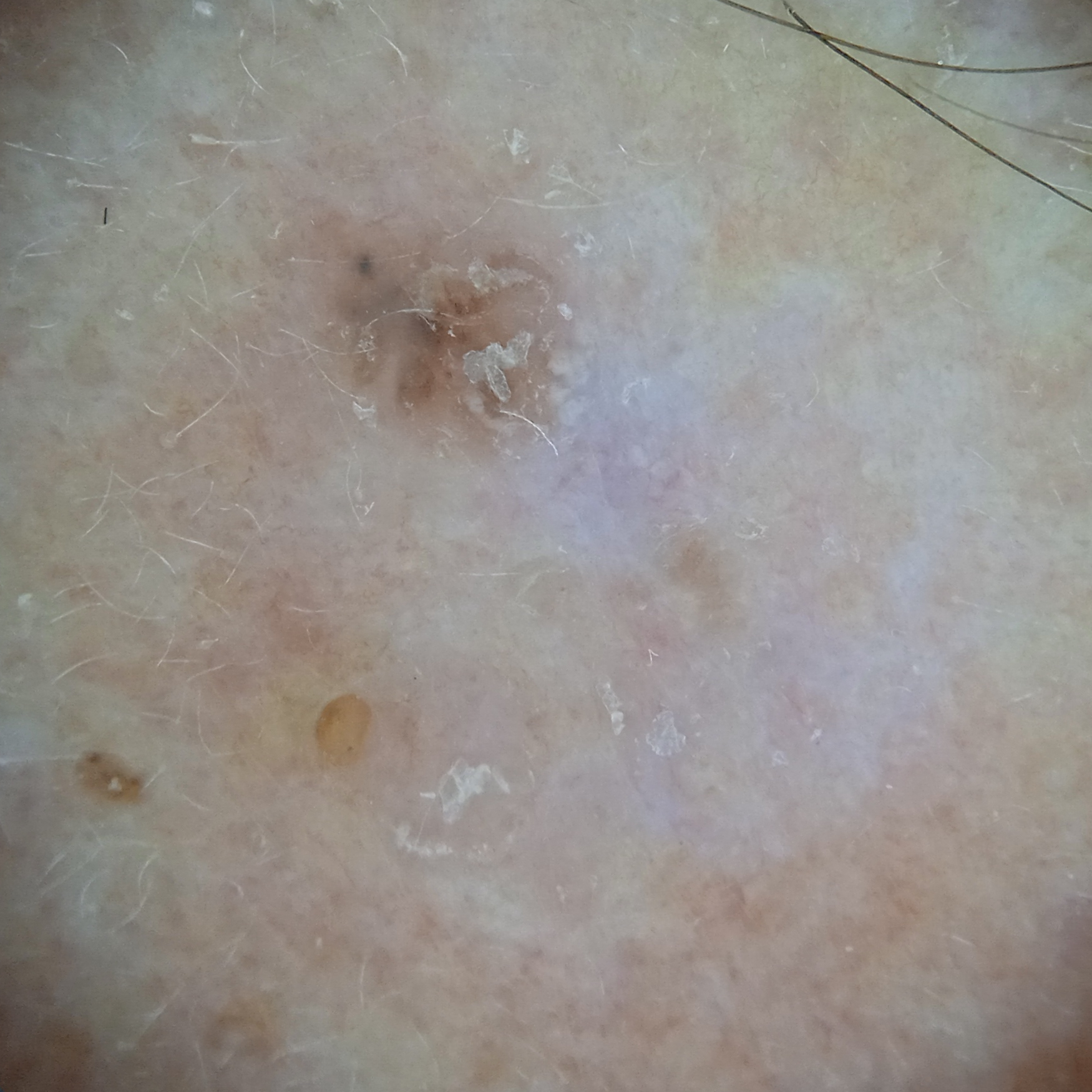Summary:
A female patient age 60. A dermoscopic image of a skin lesion. Few moles overall by the patient's own estimate. The referring clinician suspected basal cell carcinoma. The patient reports a personal history of cancer and a personal history of skin cancer. The lesion involves the face.
Pathology:
On biopsy, the diagnosis was a basal cell carcinoma, following excision, with a measured tumor thickness of 1 mm.